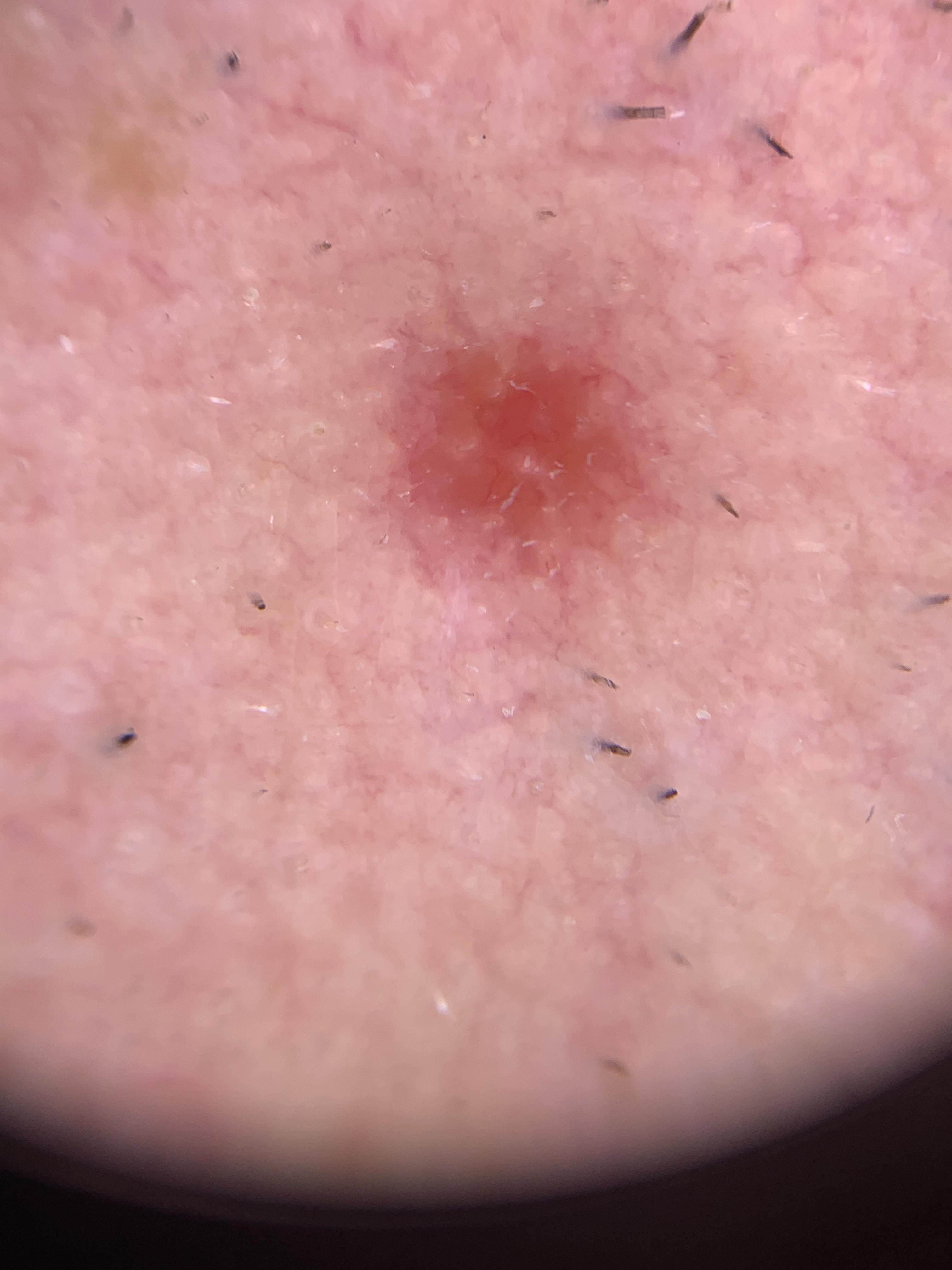patient:
  age_approx: 70
  sex: male
image: contact-polarized dermoscopy
lesion_location:
  region: the head or neck
diagnosis:
  name: Basal cell carcinoma
  malignancy: malignant
  confirmation: histopathology
  lineage: adnexal